The subject is a female aged 50–59 · this image was taken at a distance · the affected area is the leg, back of the hand and arm:
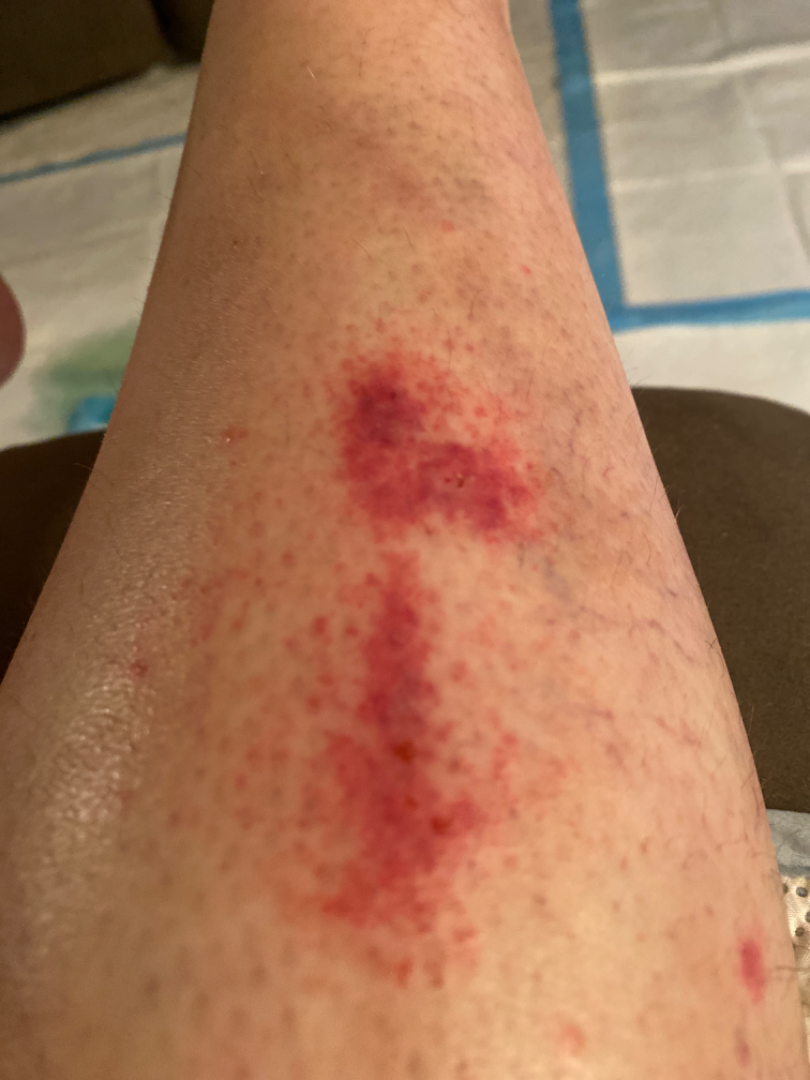The case was difficult to assess from the available photograph.
Symptoms reported: darkening, itching, bothersome appearance and enlargement.
The patient considered this a rash.
Texture is reported as rough or flaky and raised or bumpy.
The condition has been present for less than one week.